An image taken at an angle.
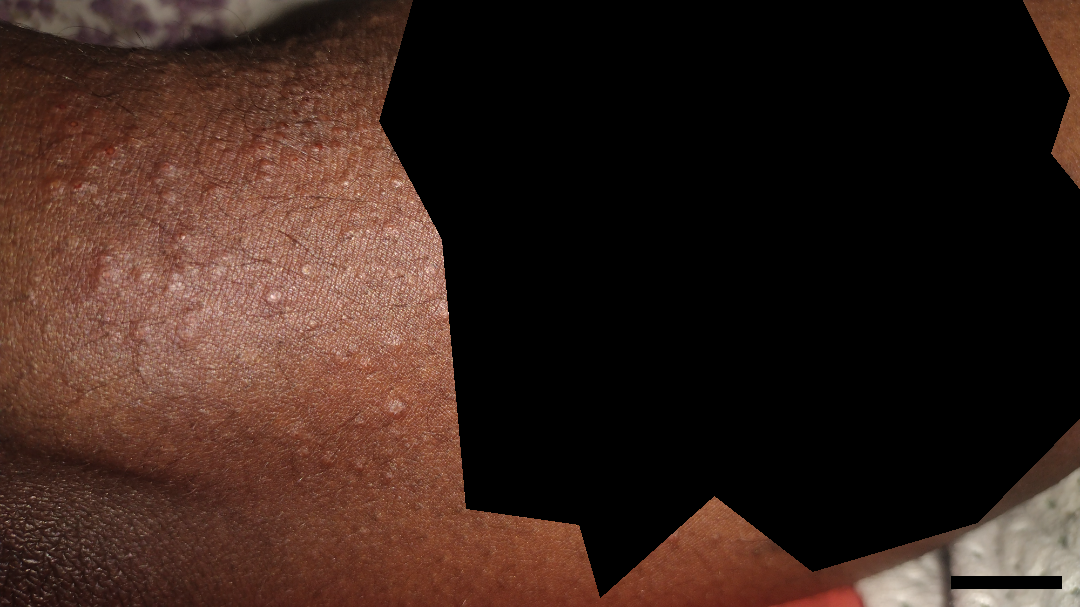Review: On photographic review: most consistent with Lichen nitidus.